A dermatoscopic image of a skin lesion.
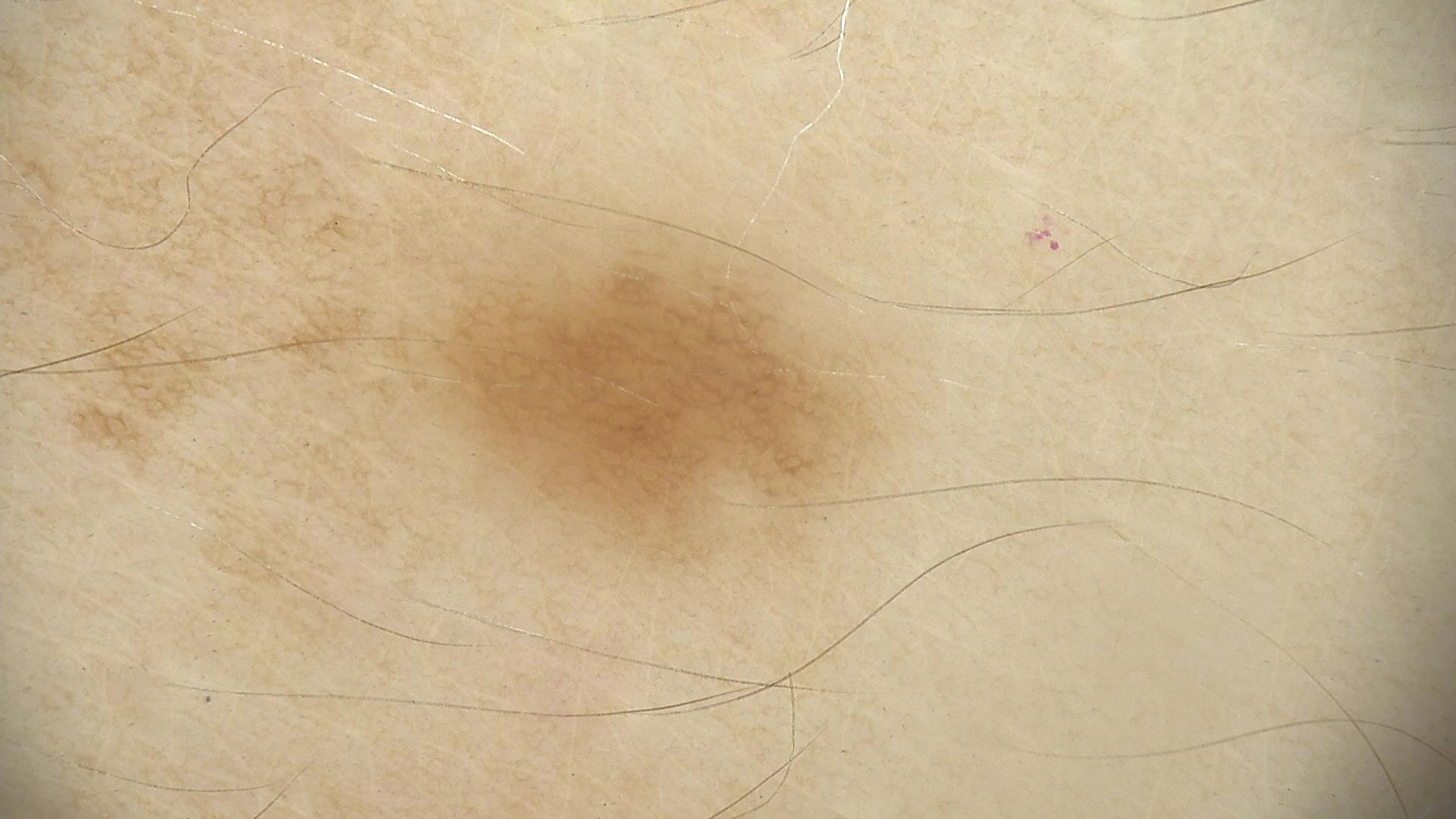• diagnostic label · lentigo simplex (expert consensus)